A dermoscopic image of a skin lesion.
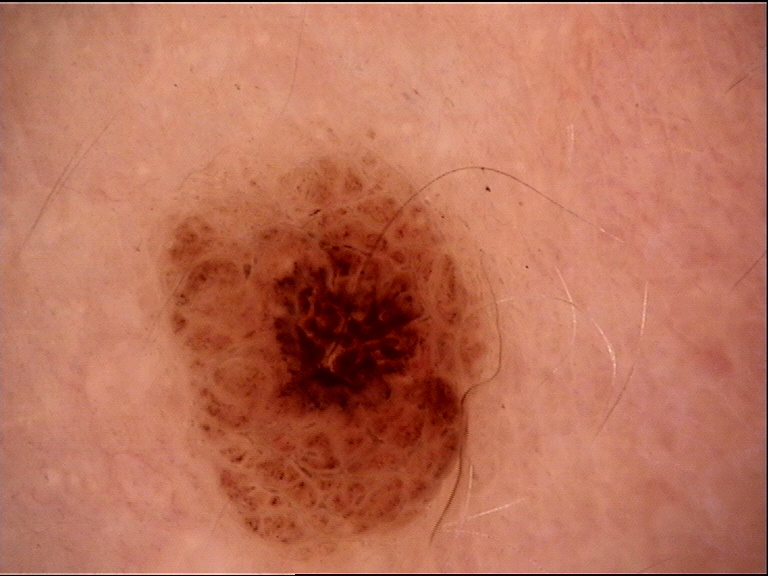Summary: The architecture is that of a banal lesion. Impression: Consistent with a compound nevus.